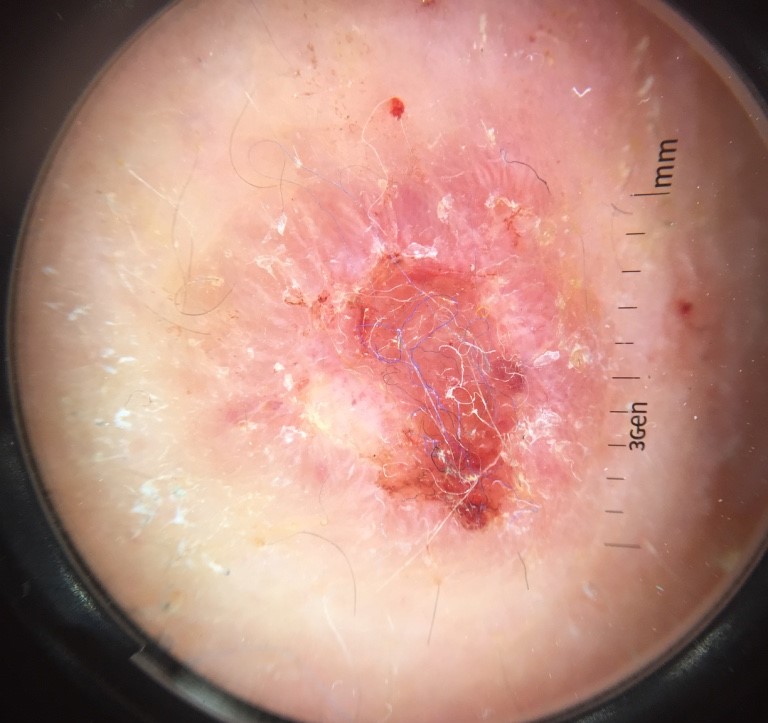Histopathology confirmed a malignancy — a squamous cell carcinoma.